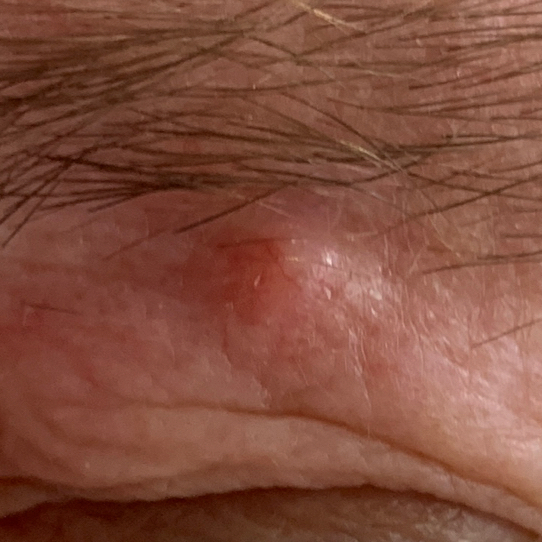A female patient in their late 50s.
By history, prior malignancy (patient or family) and prior skin cancer (patient or family).
Recorded as FST II.
A clinical photo of a skin lesion taken with a smartphone.
The lesion involves the face.
The lesion measures 6 × 4 mm.
Per patient report, the lesion is elevated, but has not bled and does not hurt.
Biopsy-confirmed as a malignancy — a basal cell carcinoma.